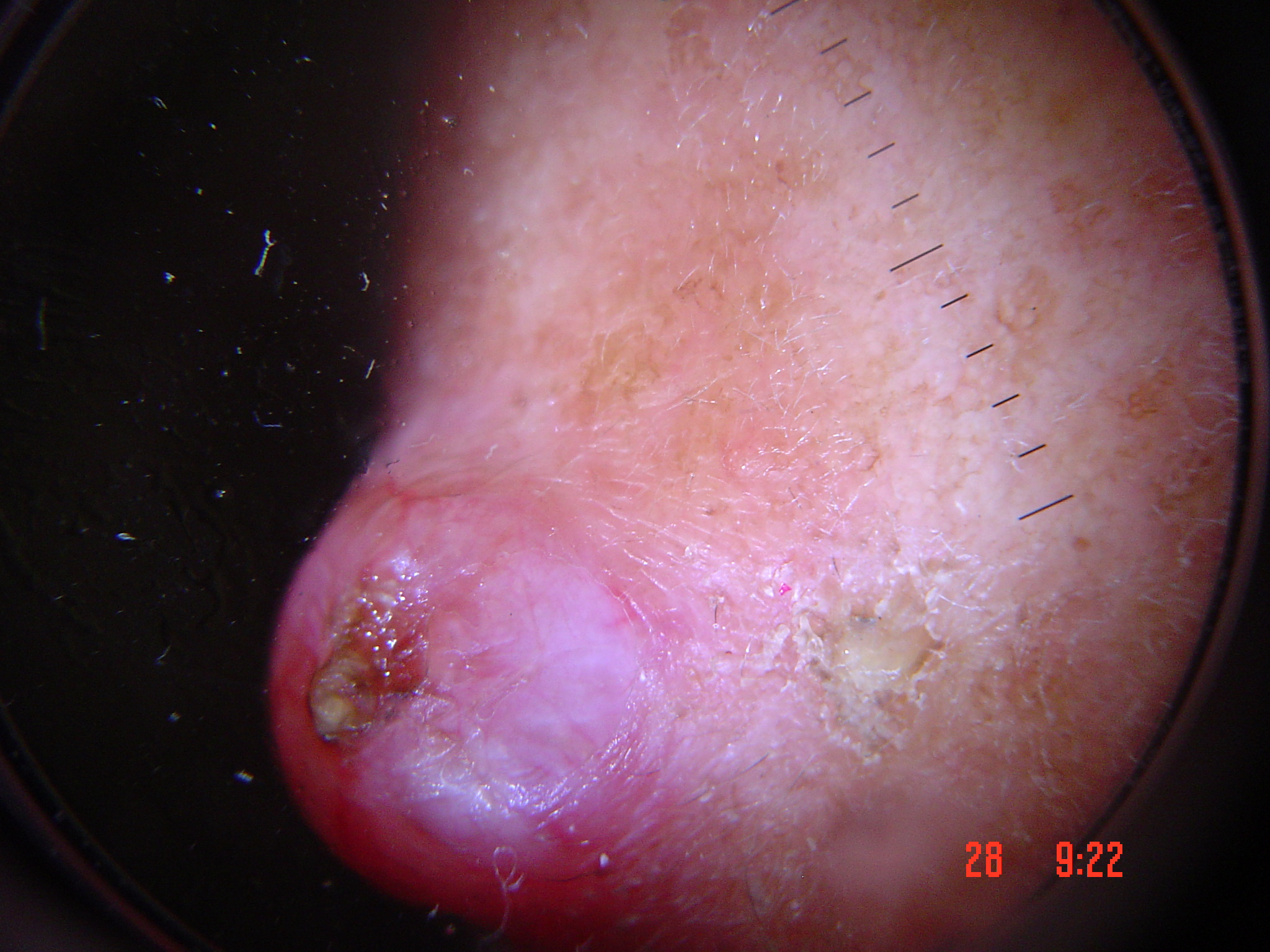diagnostic label: basal cell carcinoma (biopsy-proven).